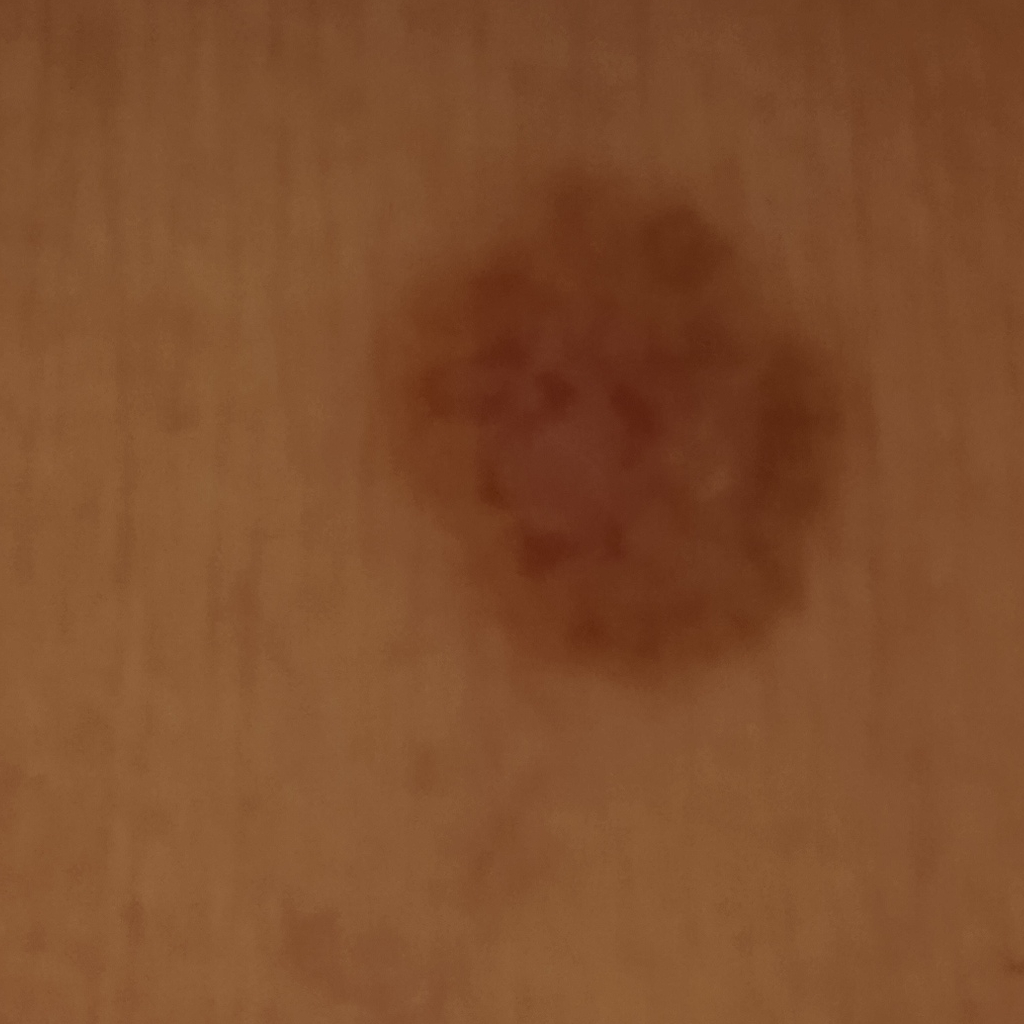sun reaction=skin tans without first burning; subject=female, aged 60; clinical context=clinical suspicion of basal cell carcinoma; imaging=clinical photograph; risk factors=a personal history of cancer, a personal history of skin cancer; nevus count=few melanocytic nevi overall; site=the torso; diameter=13.2 mm; diagnosis=basal cell carcinoma (dermatologist consensus).